A female patient 55 years of age · by self-report, immunosuppression and a prior organ transplant · a dermoscopic image of a skin lesion · imaged for a research study, with no referral diagnosis recorded · the patient describes having a moderate number of moles — 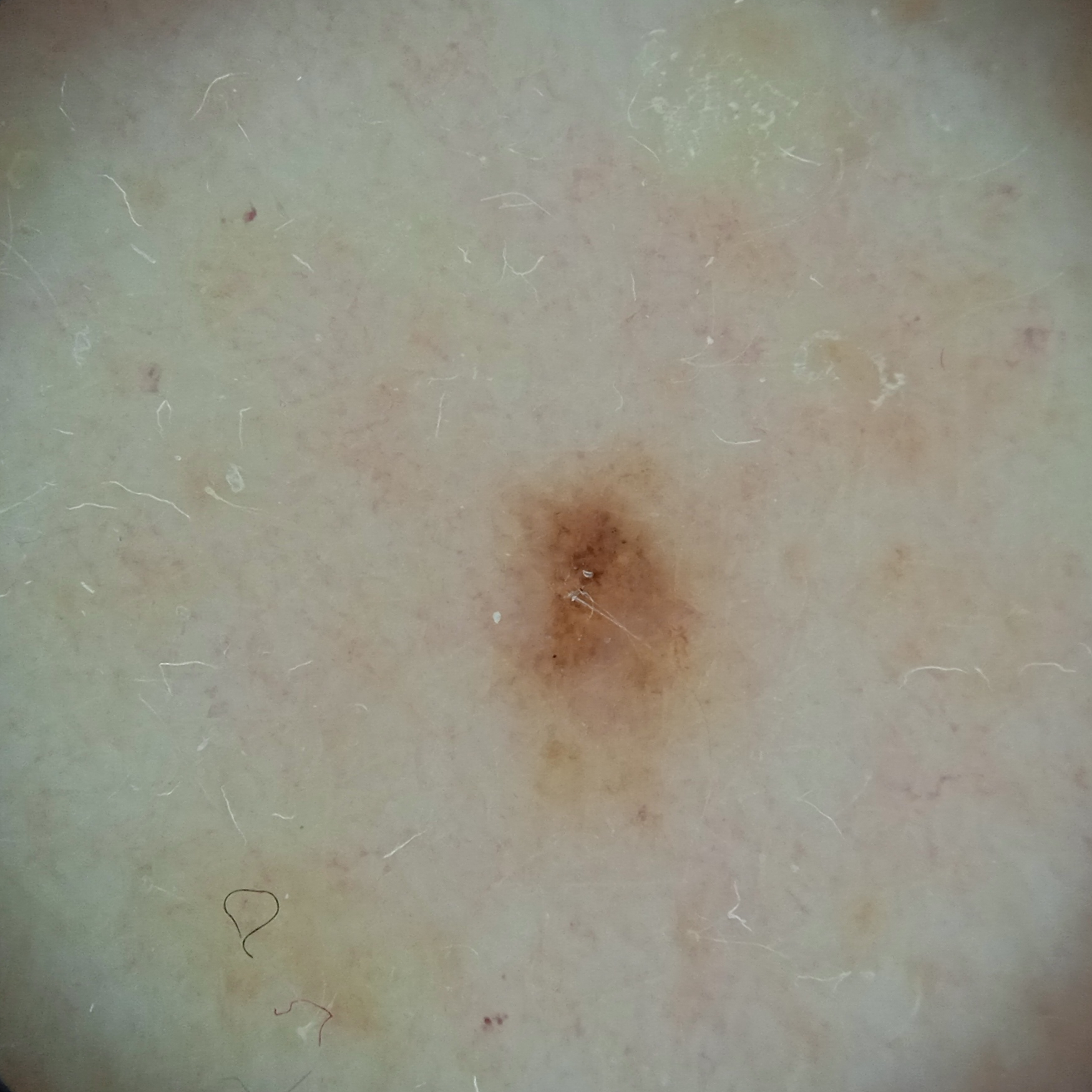  lesion_size:
    diameter_mm: 2.5
  diagnosis:
    name: melanocytic nevus
    malignancy: benign
    unanimous: false
    certainty: moderate
    second_options:
      - an atypical nevus or melanoma